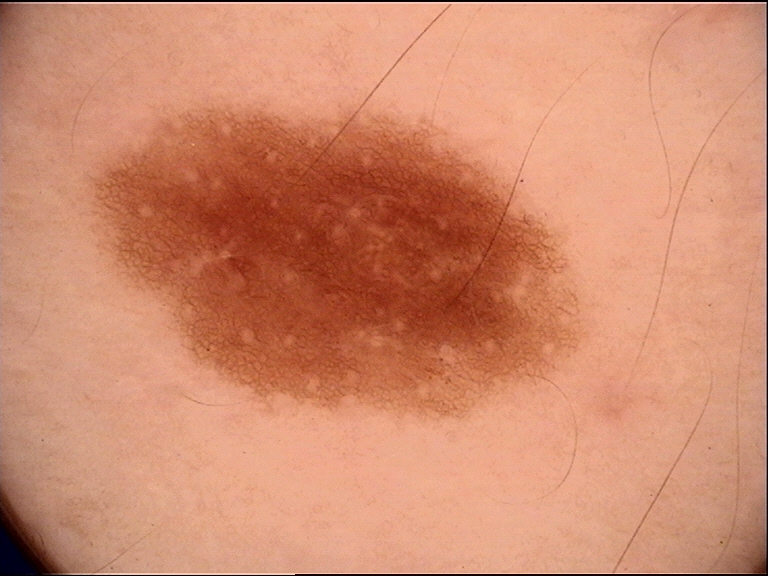A skin lesion imaged with a dermatoscope.
Diagnosed as a benign lesion — a dysplastic junctional nevus.